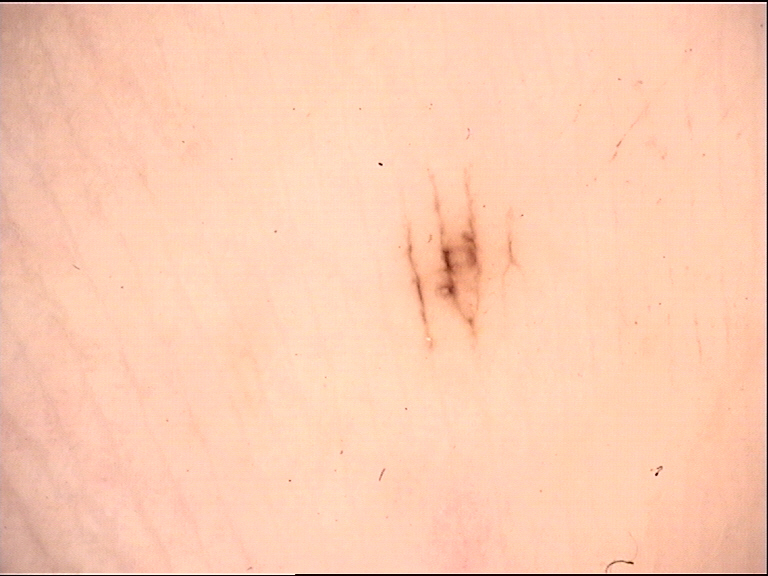The architecture is that of a banal lesion. The diagnosis was an acral junctional nevus.